A skin lesion imaged with contact-polarized dermoscopy · a male subject aged 78-82 · the patient was assessed as Fitzpatrick skin type II — 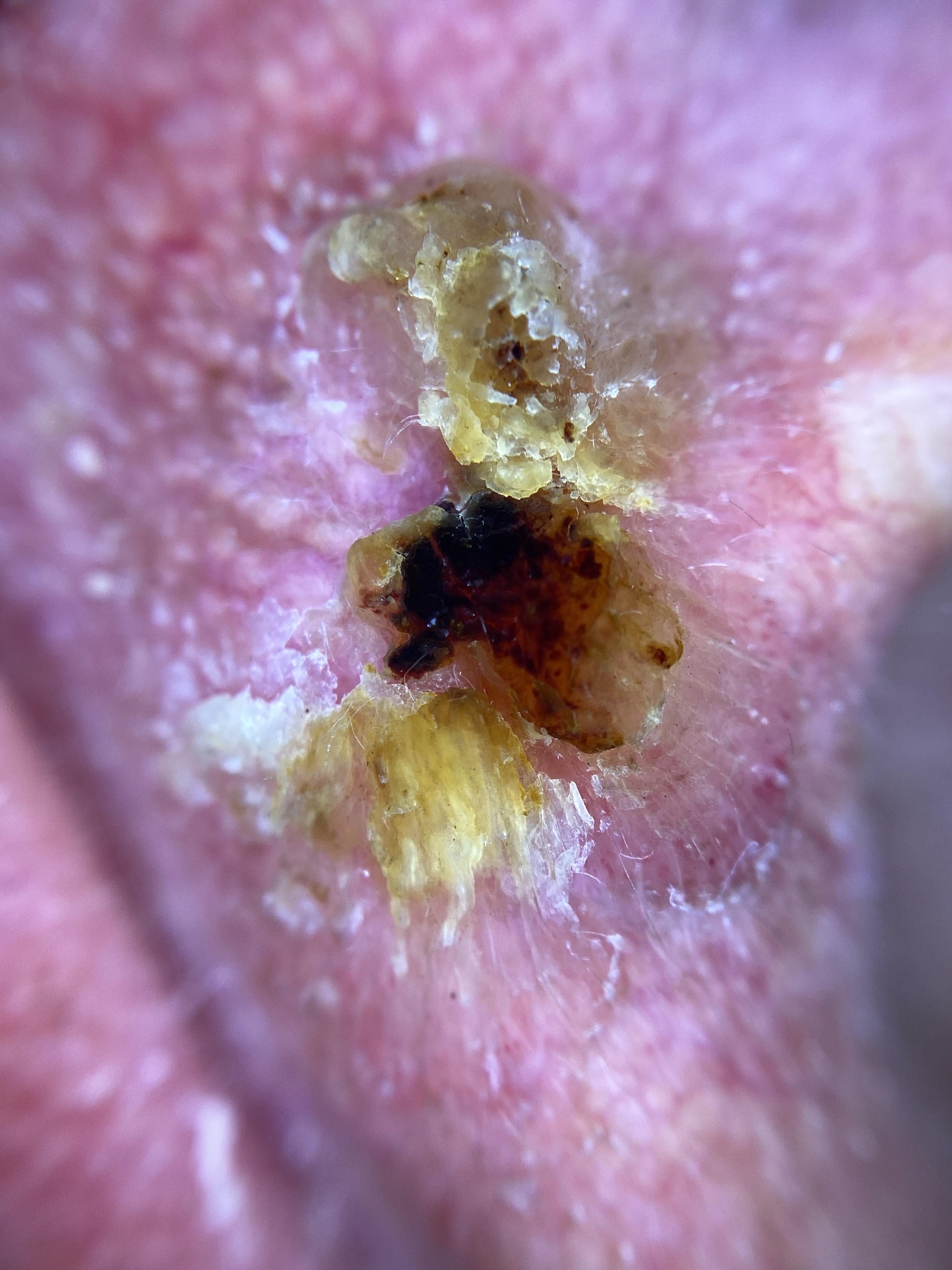Notes:
– body site · the head or neck
– diagnosis · Basal cell carcinoma (biopsy-proven)